A dermoscopic close-up of a skin lesion, a male subject approximately 70 years of age.
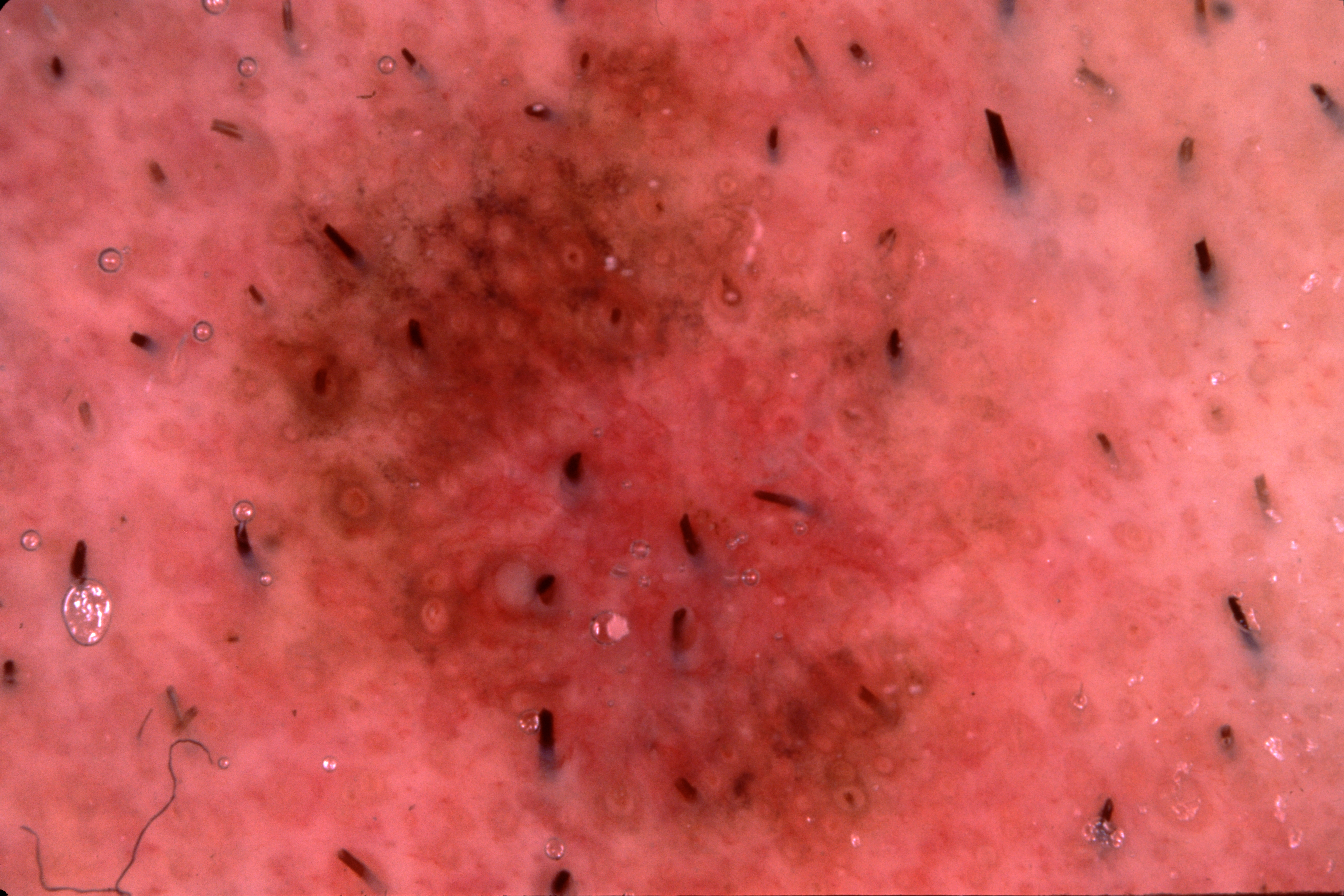Image and clinical context: Dermoscopy demonstrates no milia-like cysts, streaks, pigment network, or negative network. With coordinates (x1, y1, x2, y2), the lesion spans [225, 35, 1039, 870]. Conclusion: The biopsy diagnosis was a melanoma, a skin cancer.